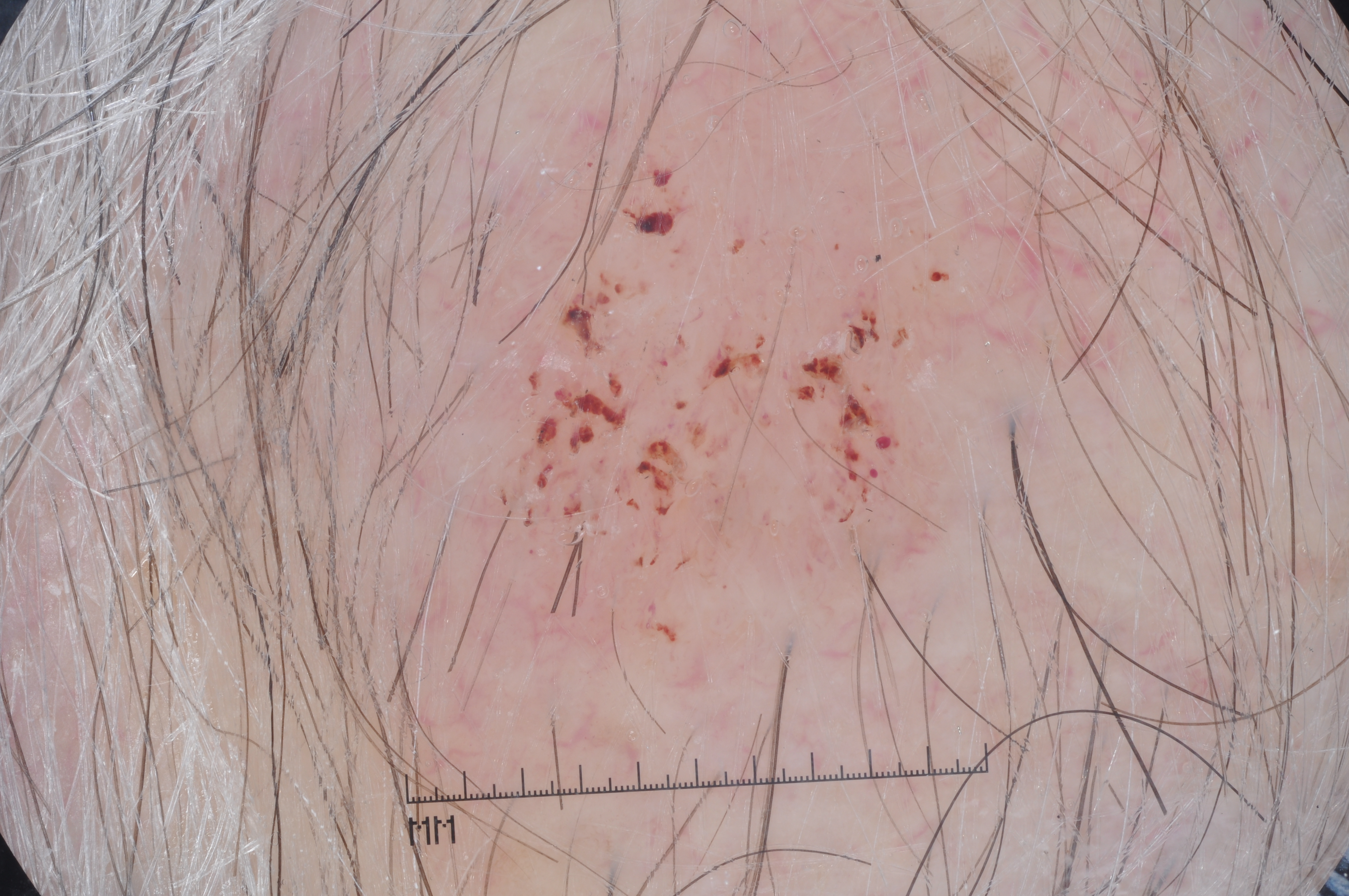A dermoscopic close-up of a skin lesion. A male patient aged 63-67. As (left, top, right, bottom), the lesion spans [475,23,992,689]. Dermoscopically, the lesion shows no negative network, milia-like cysts, streaks, or pigment network. A moderately sized lesion. The clinical diagnosis was a seborrheic keratosis.